A dermoscopic photograph of a skin lesion: 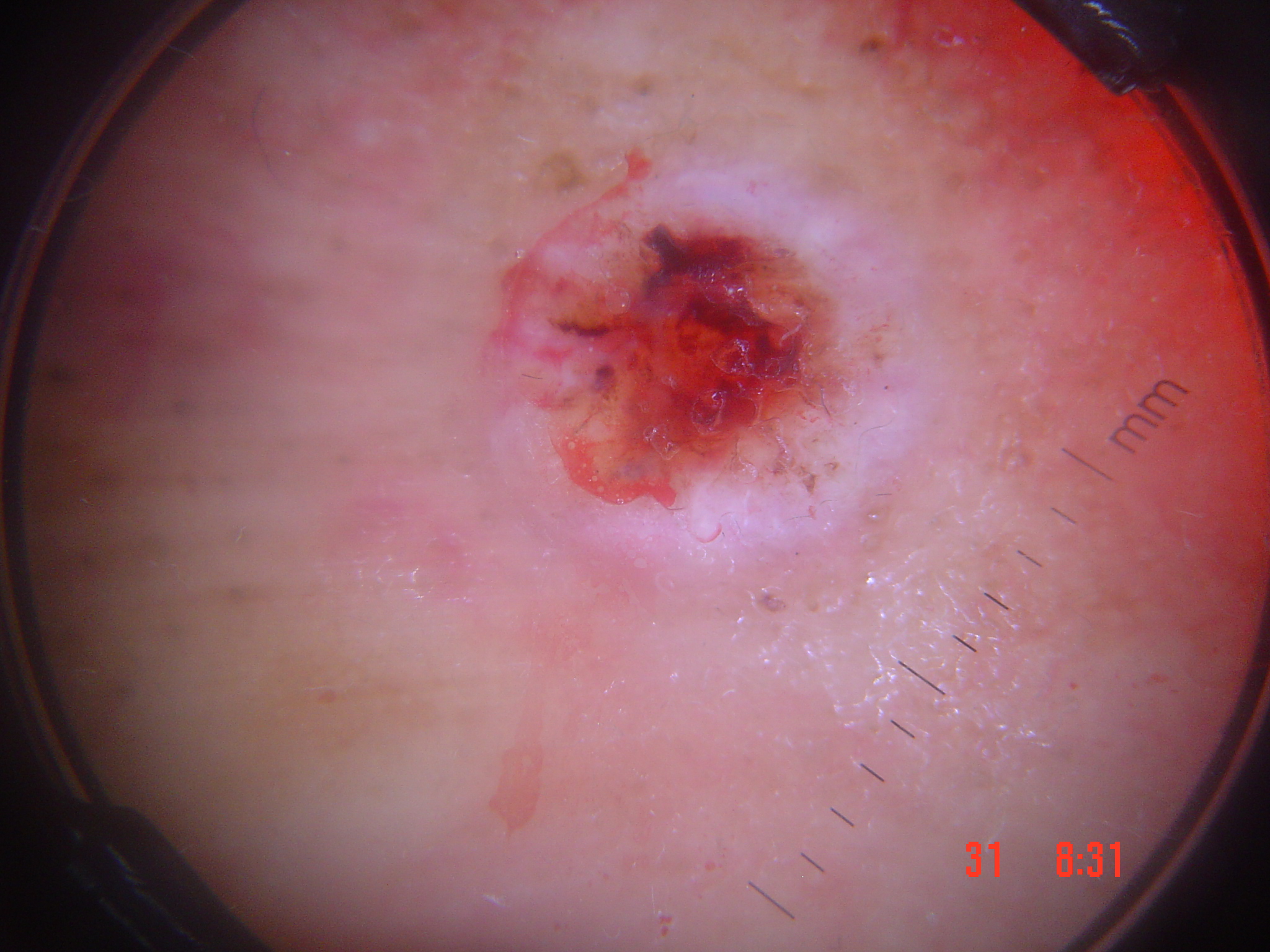Histopathologically confirmed as a keratinocytic lesion — a squamous cell carcinoma.